The subject is a female aged 50–59, the palm is involved, this is a close-up image: 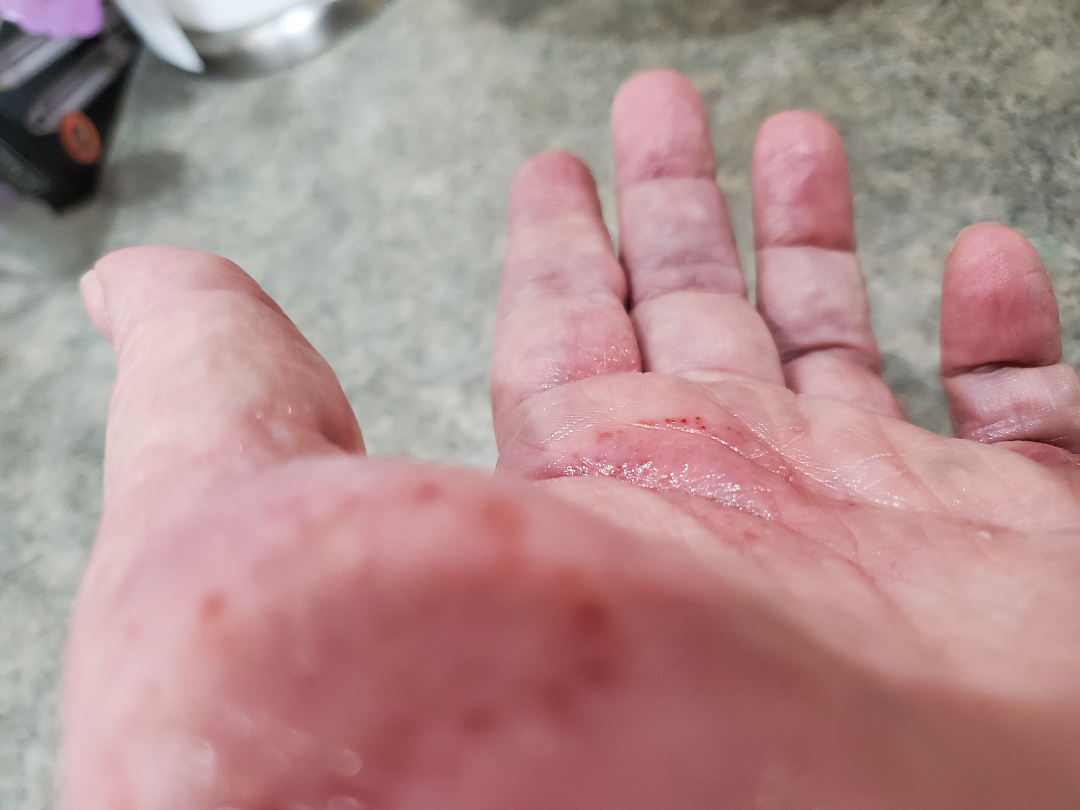Review:
Eczema and Psoriasis were considered with similar weight; less probable is Tinea.